A dermoscopy image of a single skin lesion:
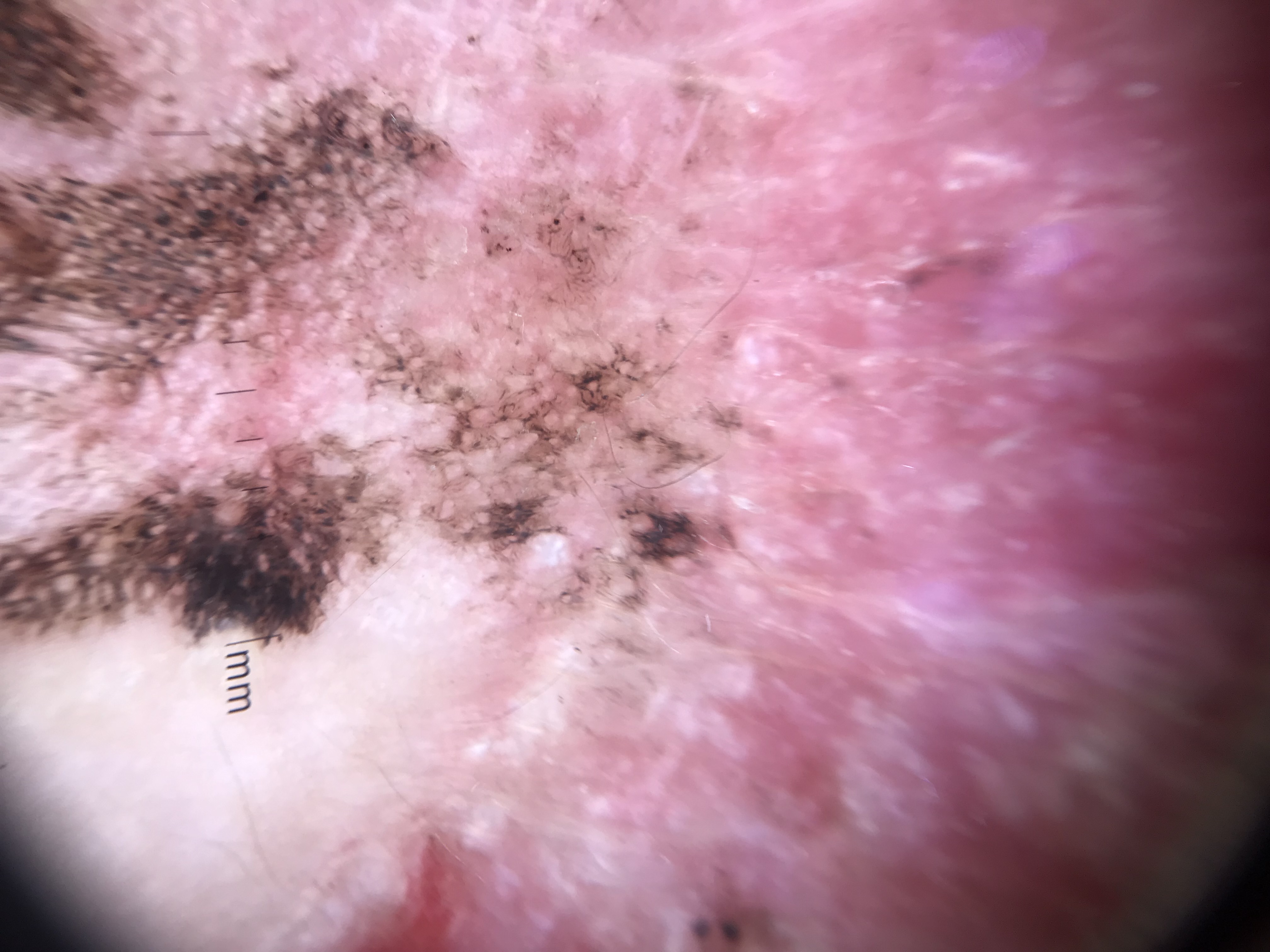class=melanoma (biopsy-proven).